A dermoscopy image of a skin lesion.
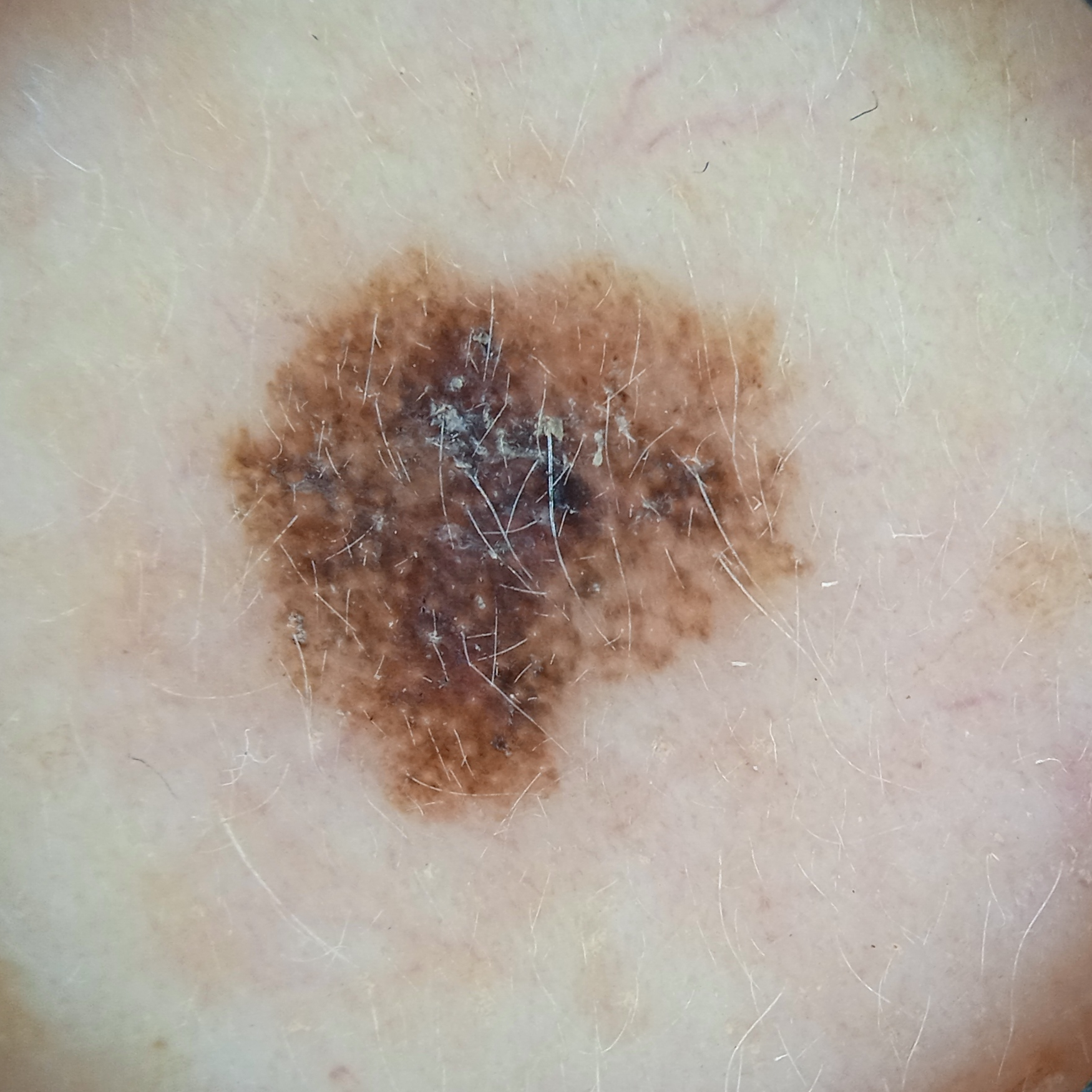The lesion is on the face.
Measuring roughly 7 mm.
Histopathology confirmed a melanoma, following excision, with a Breslow thickness of 0.4 mm.